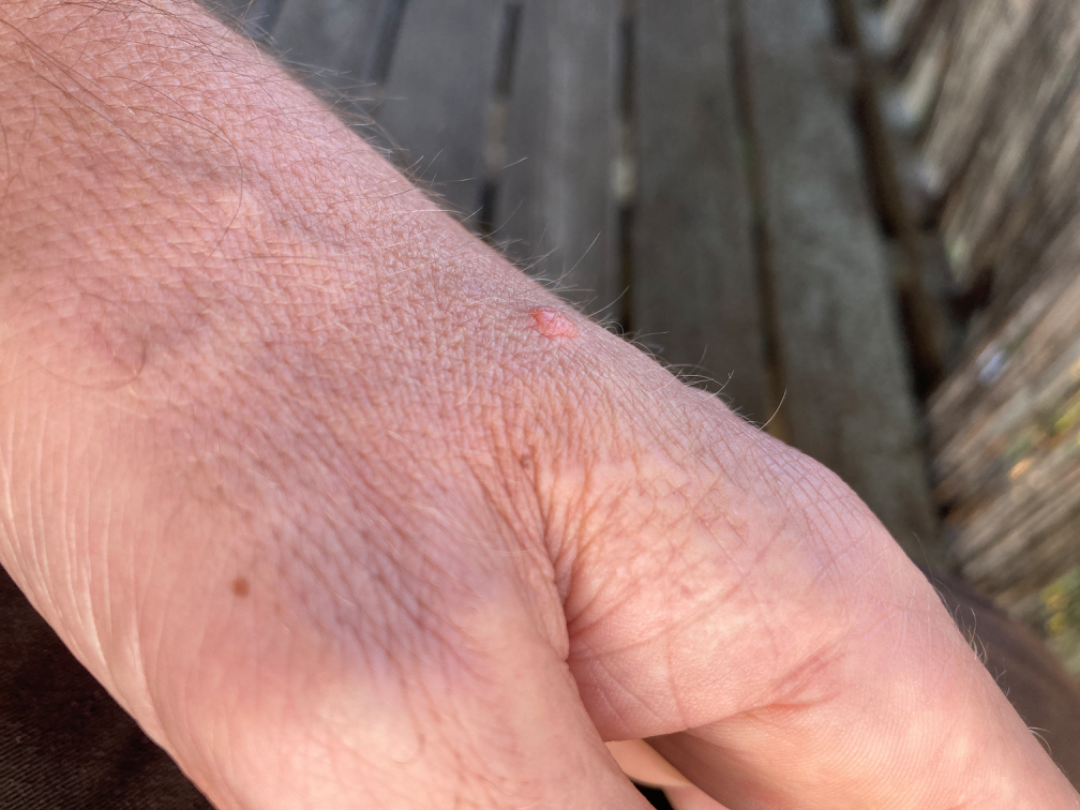Background:
An image taken at an angle.
Findings:
Melanocytic Nevus (possible); SK/ISK (possible); Verruca vulgaris (possible).